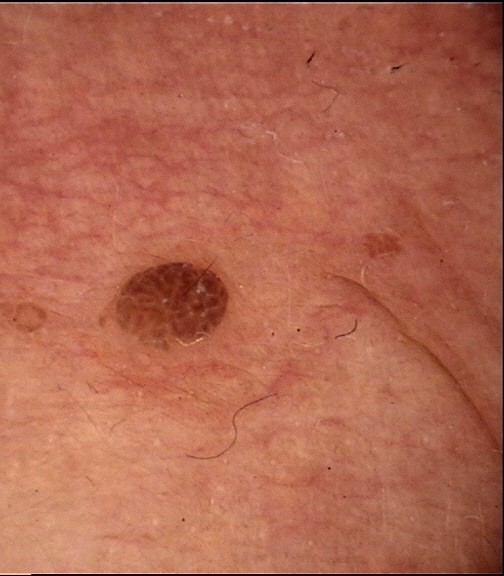| feature | finding |
|---|---|
| image type | dermoscopy |
| subtype | keratinocytic |
| diagnosis | seborrheic keratosis (expert consensus) |